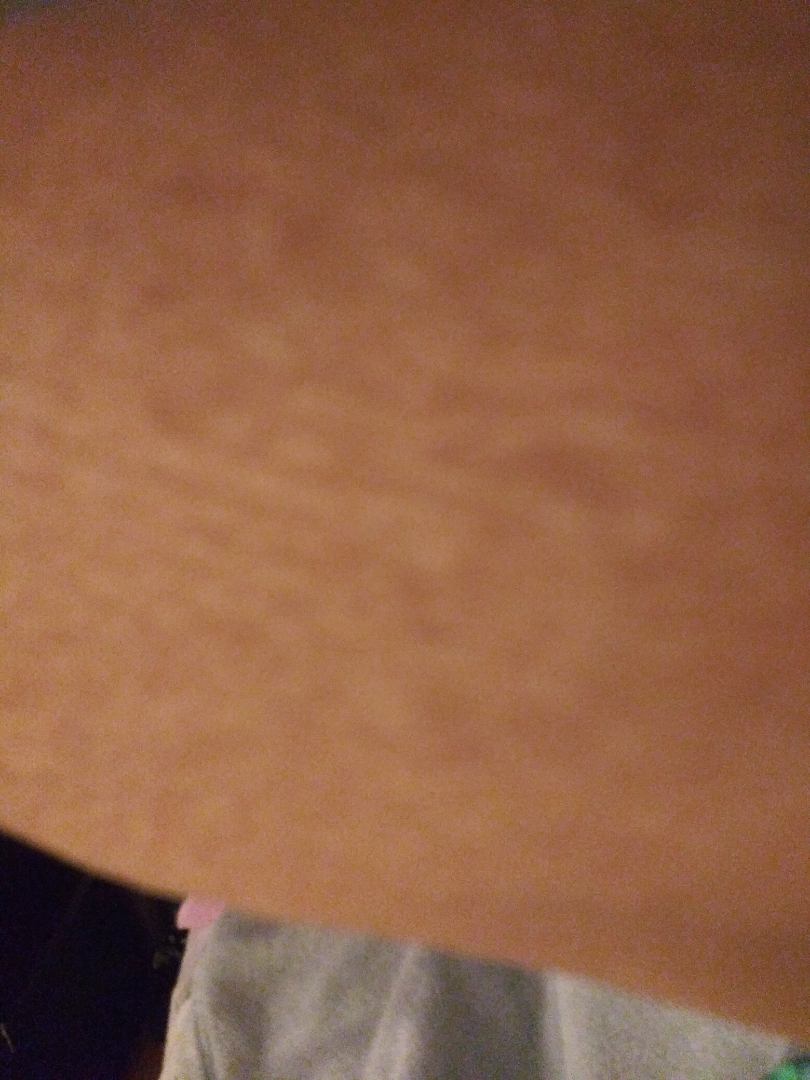The case was difficult to assess from the available photograph. The lesion involves the arm. Reported lesion symptoms include itching. The contributor notes the lesion is flat and rough or flaky. The photograph is a close-up of the affected area.